A dermoscopy image of a single skin lesion.
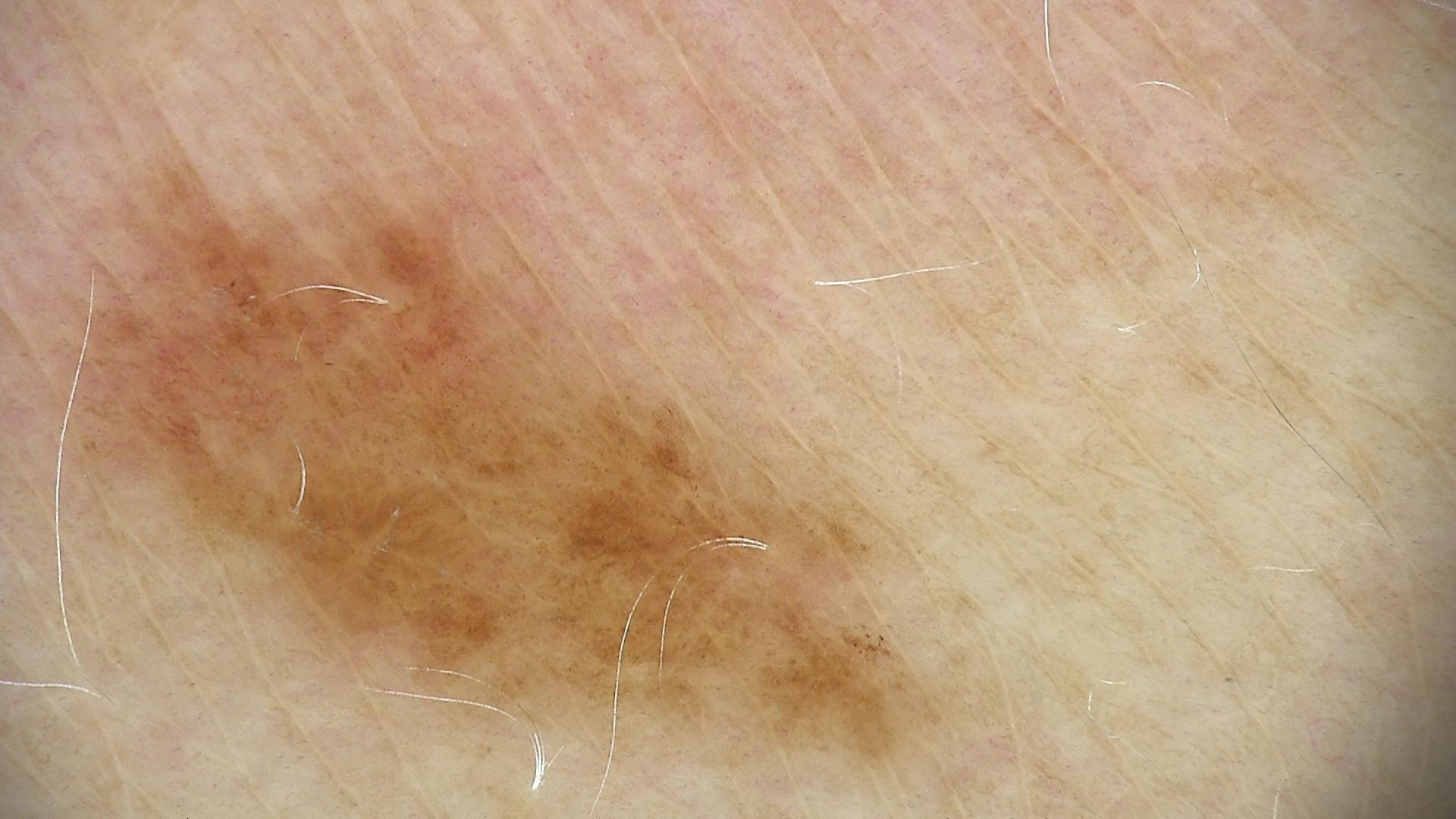{"diagnosis": {"name": "dysplastic junctional nevus", "code": "jd", "malignancy": "benign", "super_class": "melanocytic", "confirmation": "expert consensus"}}